The patient notes the condition has been present for one to four weeks · reported lesion symptoms include itching, burning, enlargement and bleeding · the patient described the issue as a rash · this is a close-up image · the arm is involved: 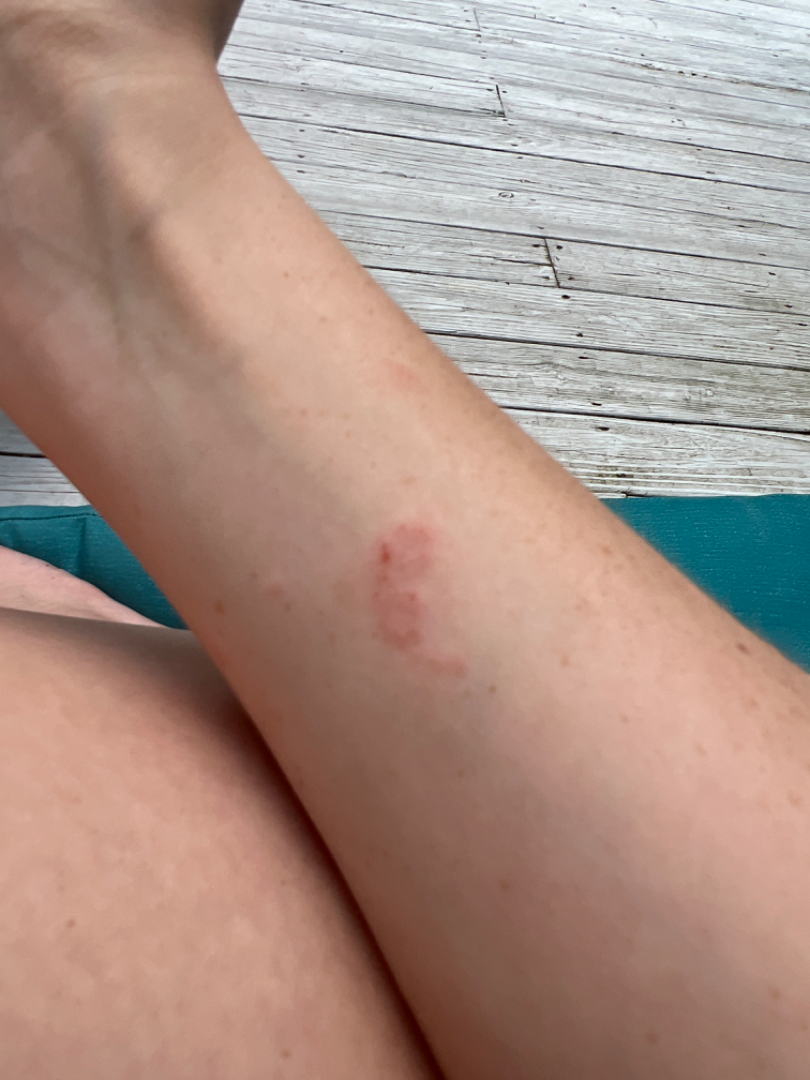  assessment: indeterminate